The contributor is a female aged 18–29 · the affected area is the back of the hand · the lesion is described as raised or bumpy · non-clinician graders estimated Monk skin tone scale 2 (US pool) or 3 (India pool) · close-up view · self-categorized by the patient as a rash: 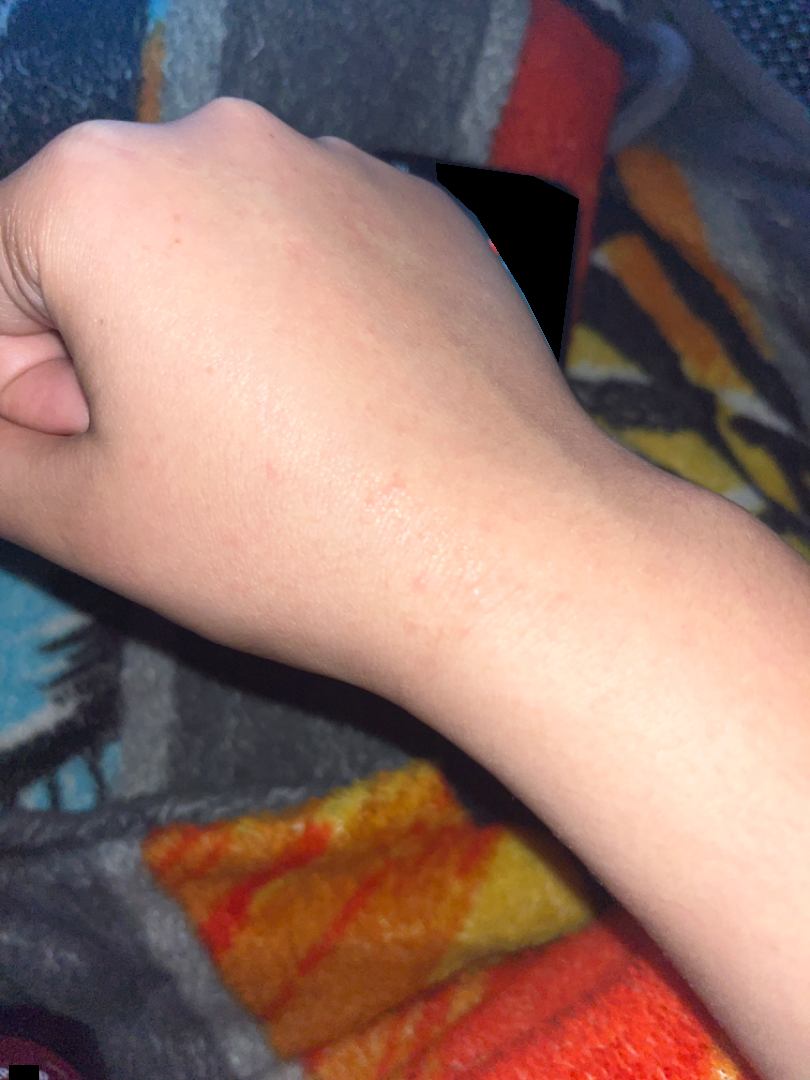Q: Could the case be diagnosed?
A: not assessable